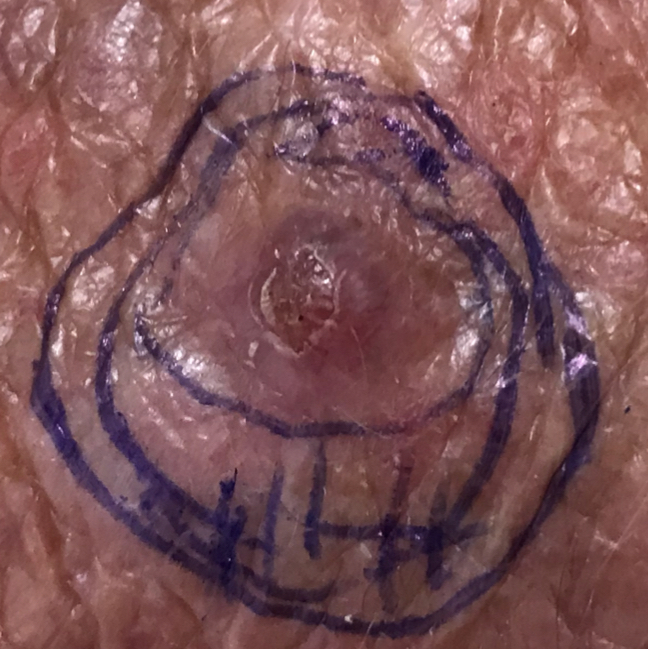A female patient aged 57.
A clinical photograph of a skin lesion.
The lesion is located on a hand.
Per patient report, the lesion is elevated, has grown, and has bled, but has not changed.
Histopathological examination showed a basal cell carcinoma.